A dermoscopic close-up of a skin lesion · a male subject, aged around 45 — 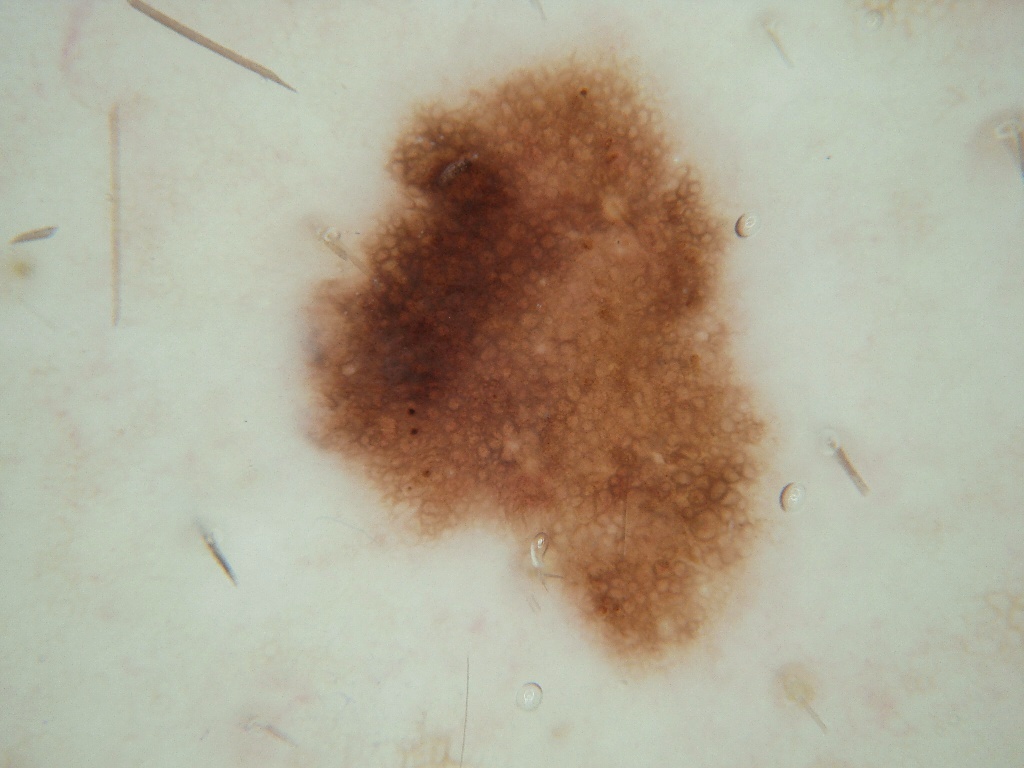Q: What dermoscopic features are present?
A: pigment network; absent: negative network, milia-like cysts, globules, and streaks
Q: Where is the lesion in the image?
A: [295,42,776,675]
Q: How much of the field does the lesion occupy?
A: moderate
Q: What is this lesion?
A: a melanocytic nevus